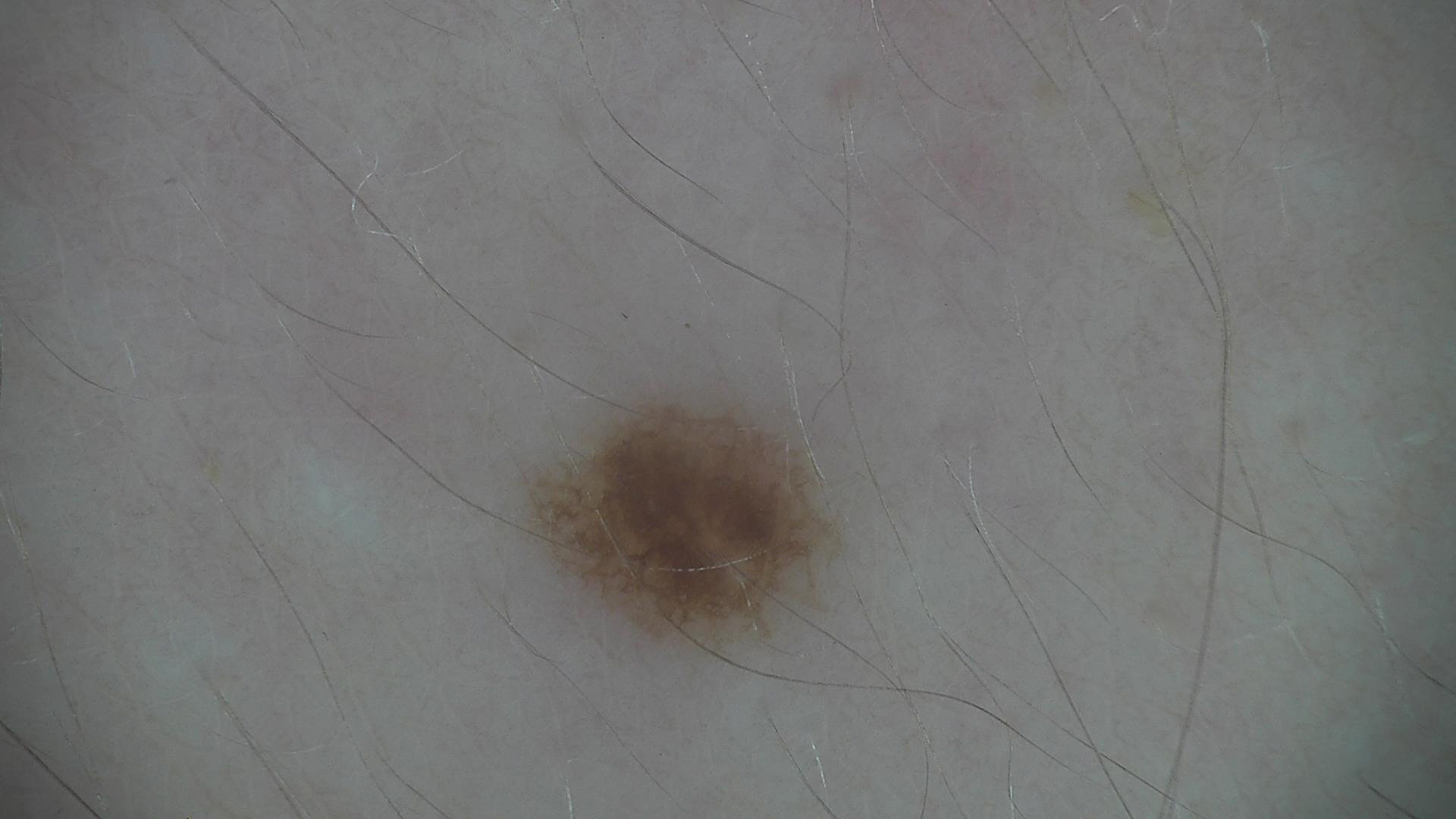Q: What is the imaging modality?
A: dermatoscopy
Q: What is this lesion?
A: dysplastic junctional nevus (expert consensus)